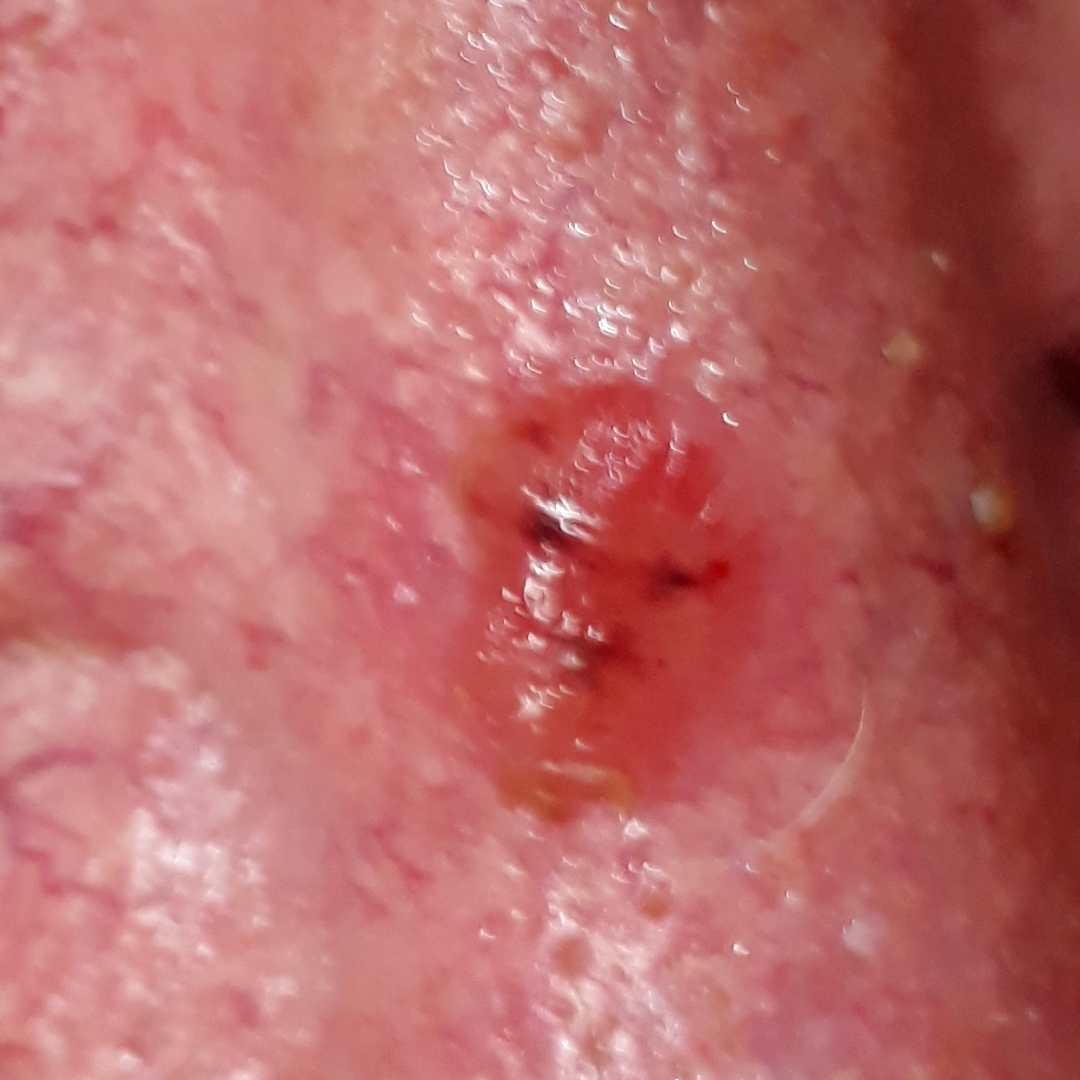<lesion>
  <patient>
    <age>74</age>
    <gender>male</gender>
  </patient>
  <symptoms>
    <present>elevation, itching, bleeding</present>
    <absent>change in appearance, growth</absent>
  </symptoms>
  <diagnosis>
    <name>basal cell carcinoma</name>
    <code>BCC</code>
    <malignancy>malignant</malignancy>
    <confirmation>histopathology</confirmation>
  </diagnosis>
</lesion>